A skin lesion imaged with a dermatoscope: 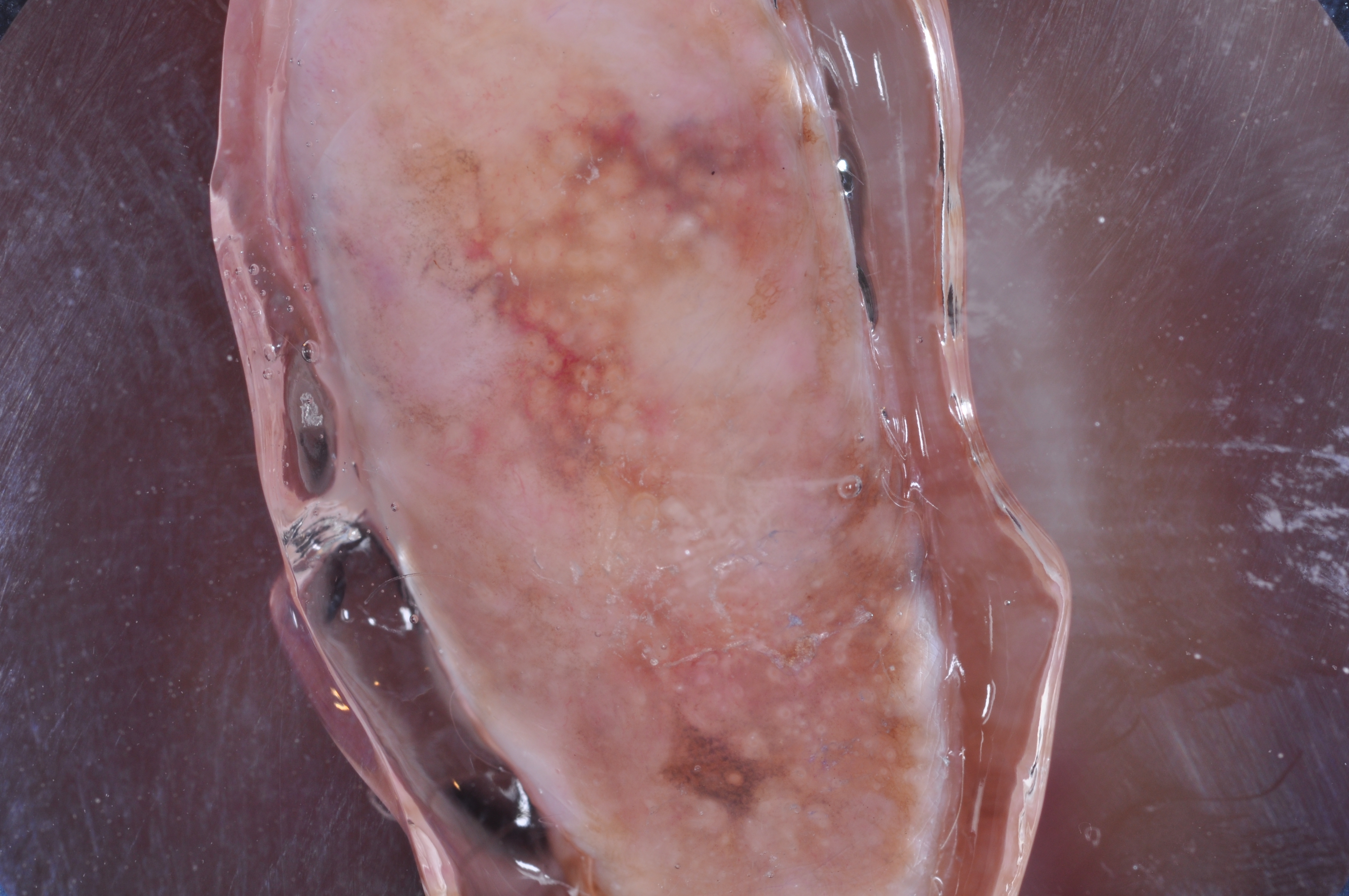Dermoscopic review identifies milia-like cysts.
As (left, top, right, bottom), the visible lesion spans <box>377, 2, 958, 873</box>.
The lesion covers approximately 30% of the dermoscopic field.
Confirmed on histopathology as a melanoma.